The leg is involved · this is a close-up image:
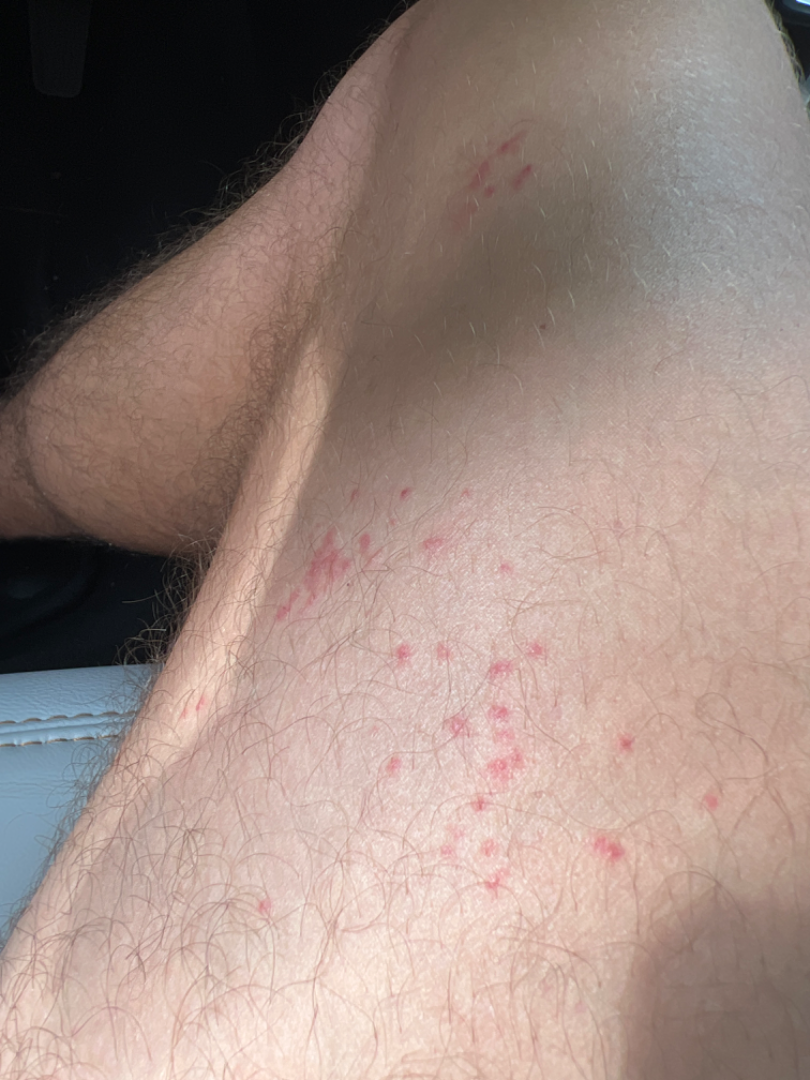| key | value |
|---|---|
| assessment | indeterminate from the photograph |